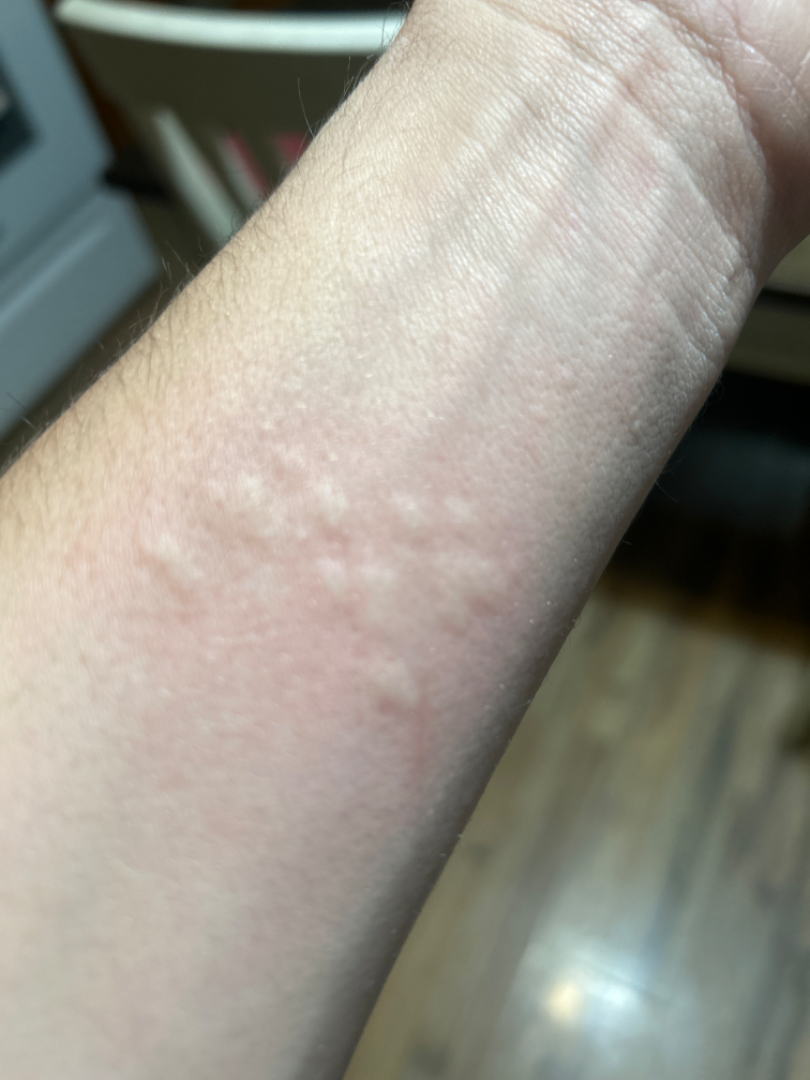Case summary:
– view — close-up
– differential — consistent with Urticaria